A female subject age 26; the patient says their skin reddens with sun exposure; the patient reports a history of sunbed use; a macroscopic clinical photograph of a skin lesion; collected as part of a research study, without a referral diagnosis.
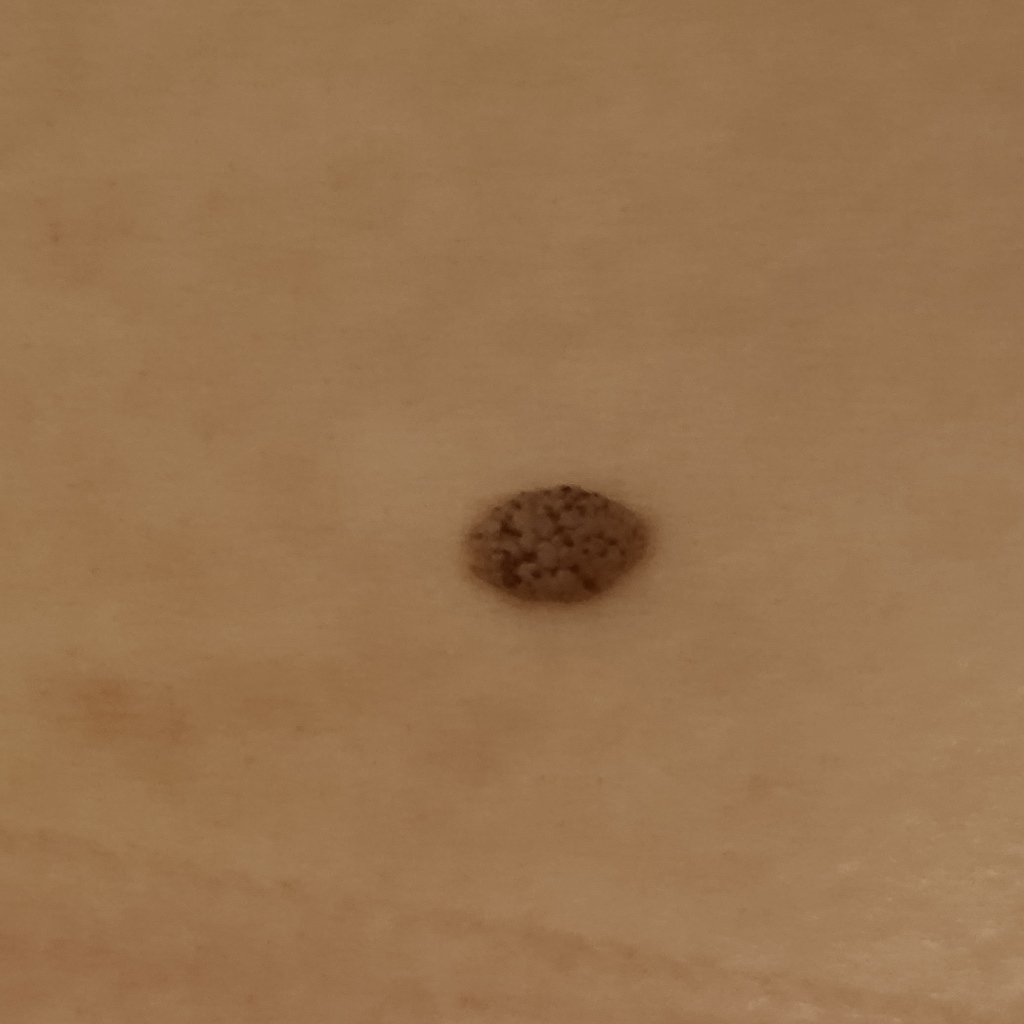The lesion is on the back. The lesion is about 8.4 mm across. The diagnostic impression was a seborrheic keratosis.